Located on the leg and front of the torso. The subject is 18–29, female. An image taken at a distance: 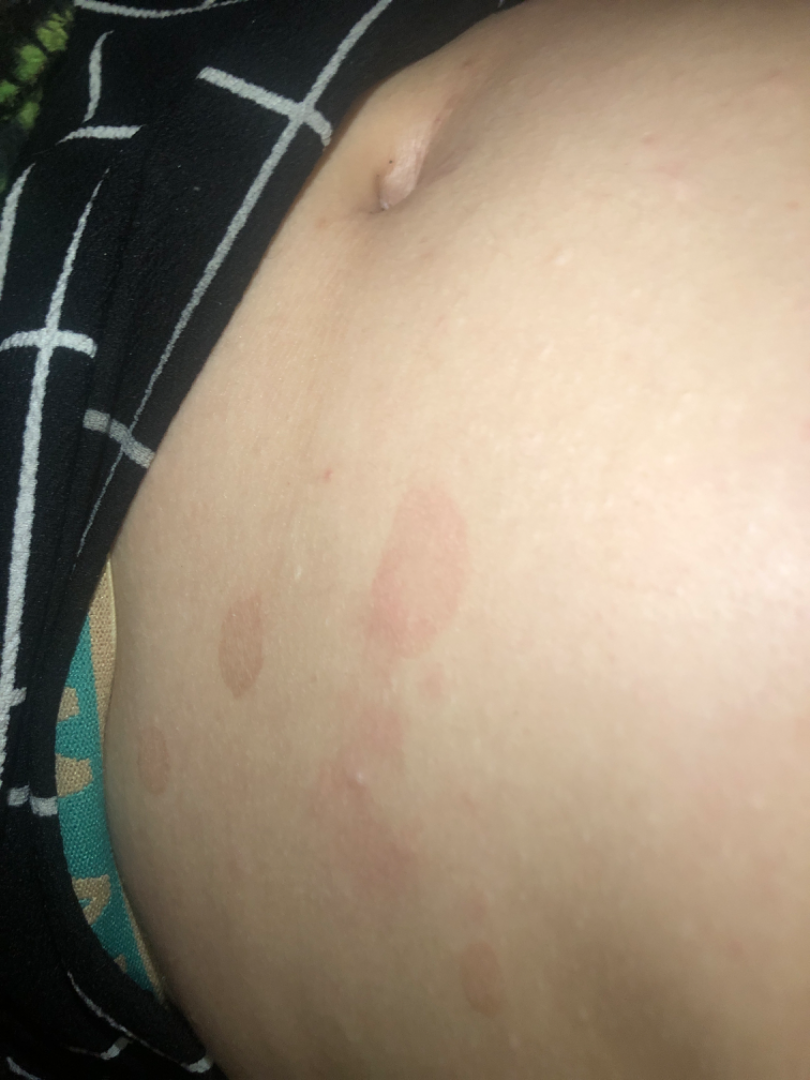dermatologist impression — one reviewing dermatologist: Parapsoriasis, Syphilis and Seborrheic Dermatitis were each considered, in no particular order.